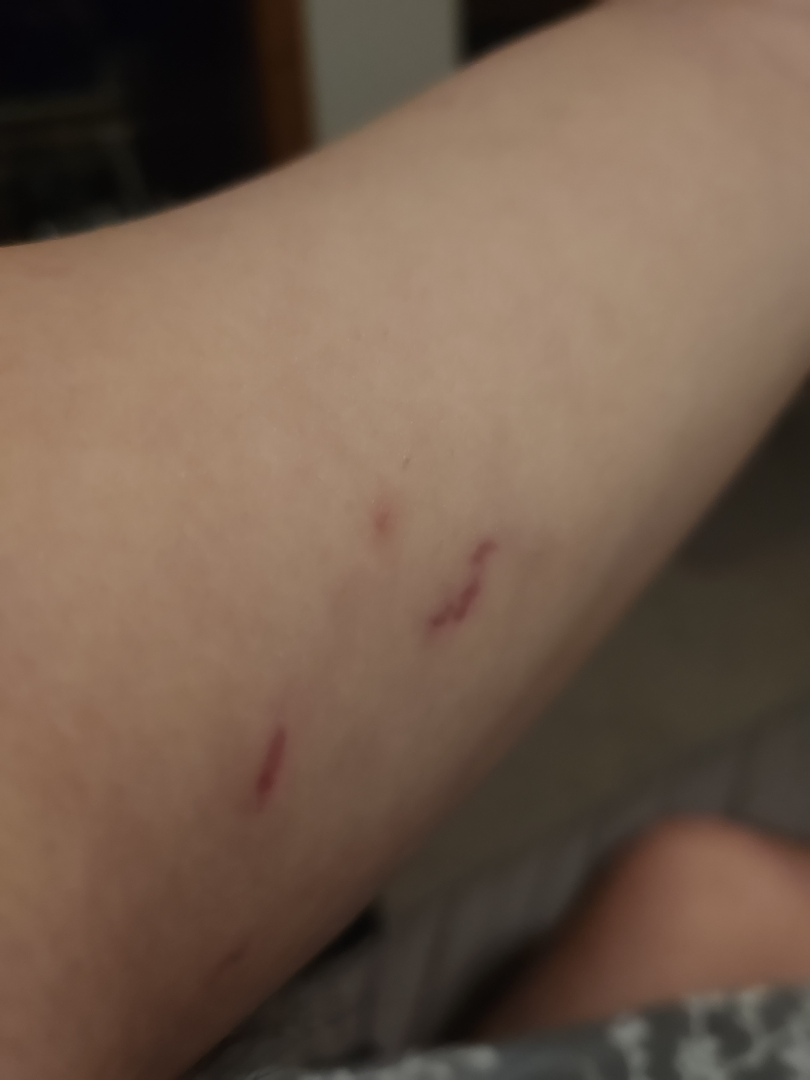History: The arm is involved. The photograph was taken at an angle. Impression: Abrasion, scrape, or scab; Skin striae; and Animal bite - wound were each considered, in no particular order.